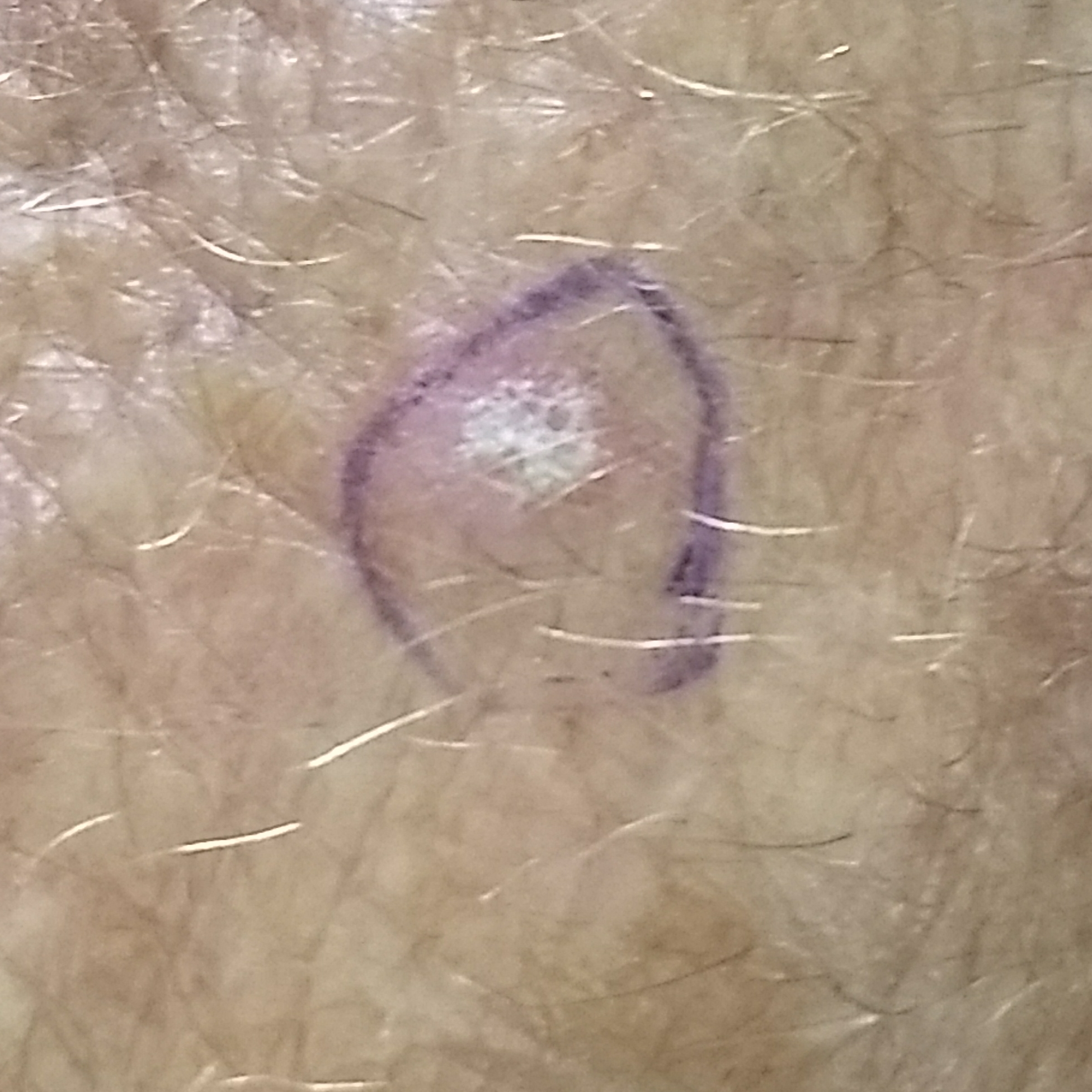A subject in their 60s. The lesion involves a hand. By the patient's account, the lesion itches. Consistent with an actinic keratosis.